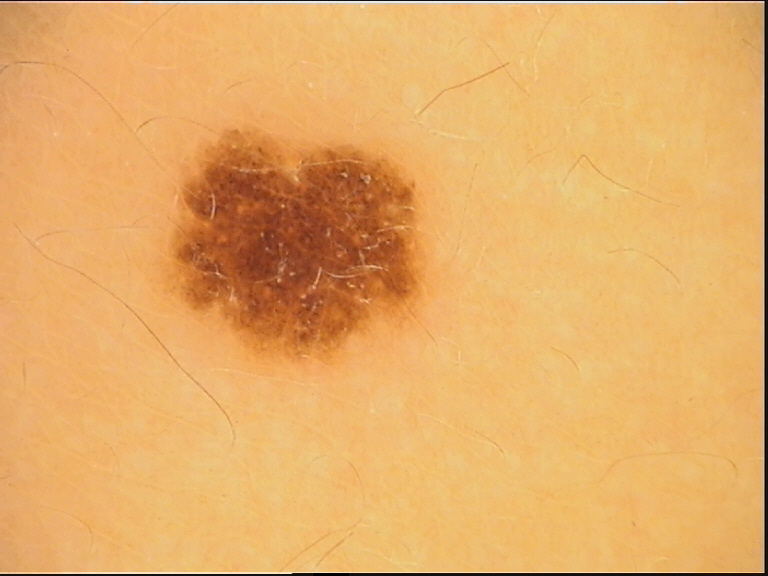A dermoscopic image of a skin lesion. Consistent with a benign lesion — a dysplastic junctional nevus.